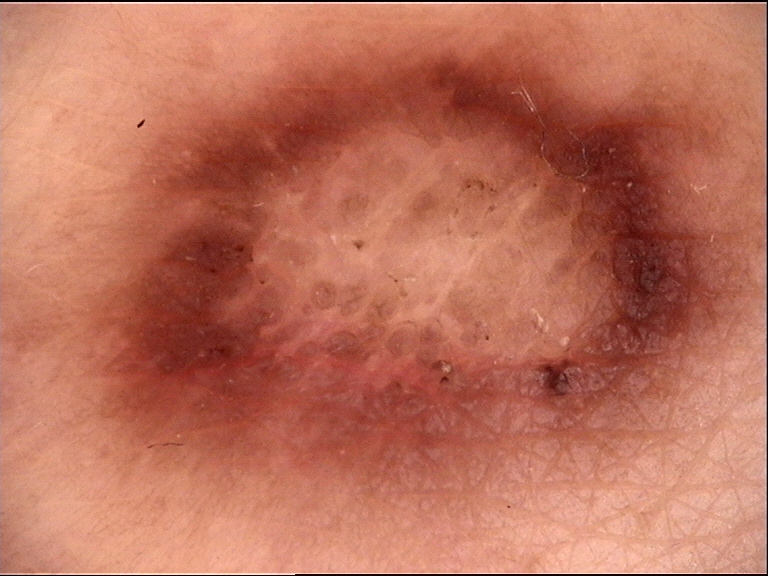Findings:
A dermoscopic photograph of a skin lesion. The morphology is that of a fibro-histiocytic lesion.
Impression:
The diagnosis was a dermatofibroma.